This is a dermoscopic photograph of a skin lesion. The subject is a male aged around 65.
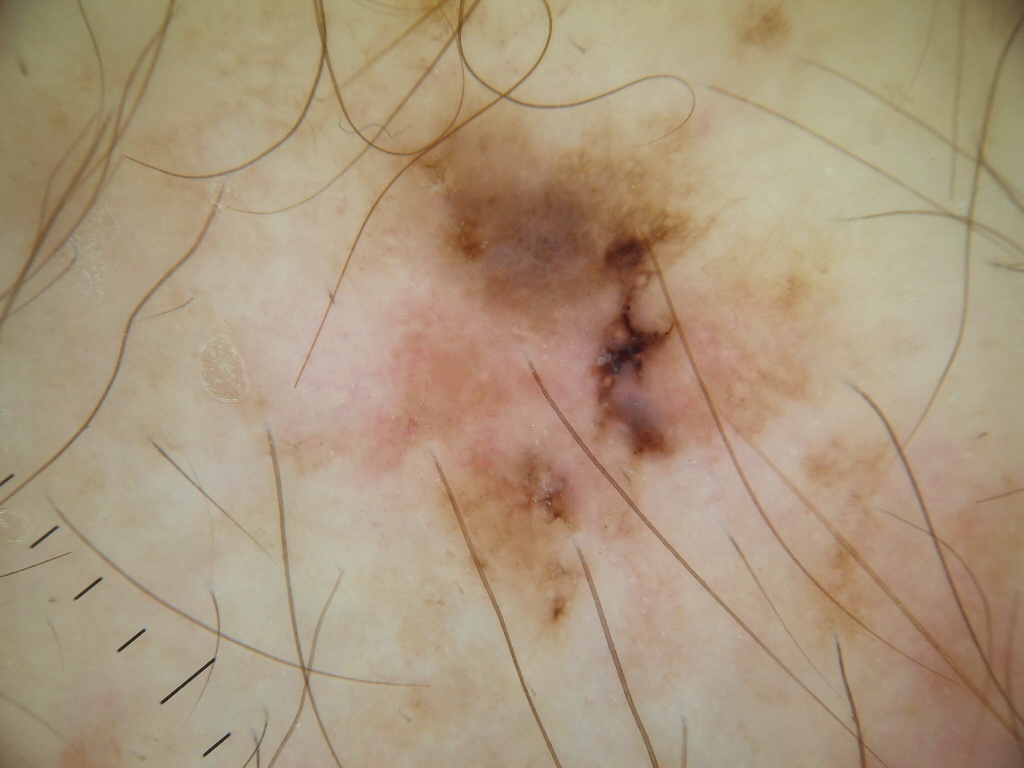Findings:
Dermoscopic assessment notes pigment network and globules, with no milia-like cysts, streaks, or negative network. With coordinates (x1, y1, x2, y2), the lesion is bounded by <box>292, 77, 826, 646</box>.
Diagnosis:
Histopathological examination showed a melanoma.